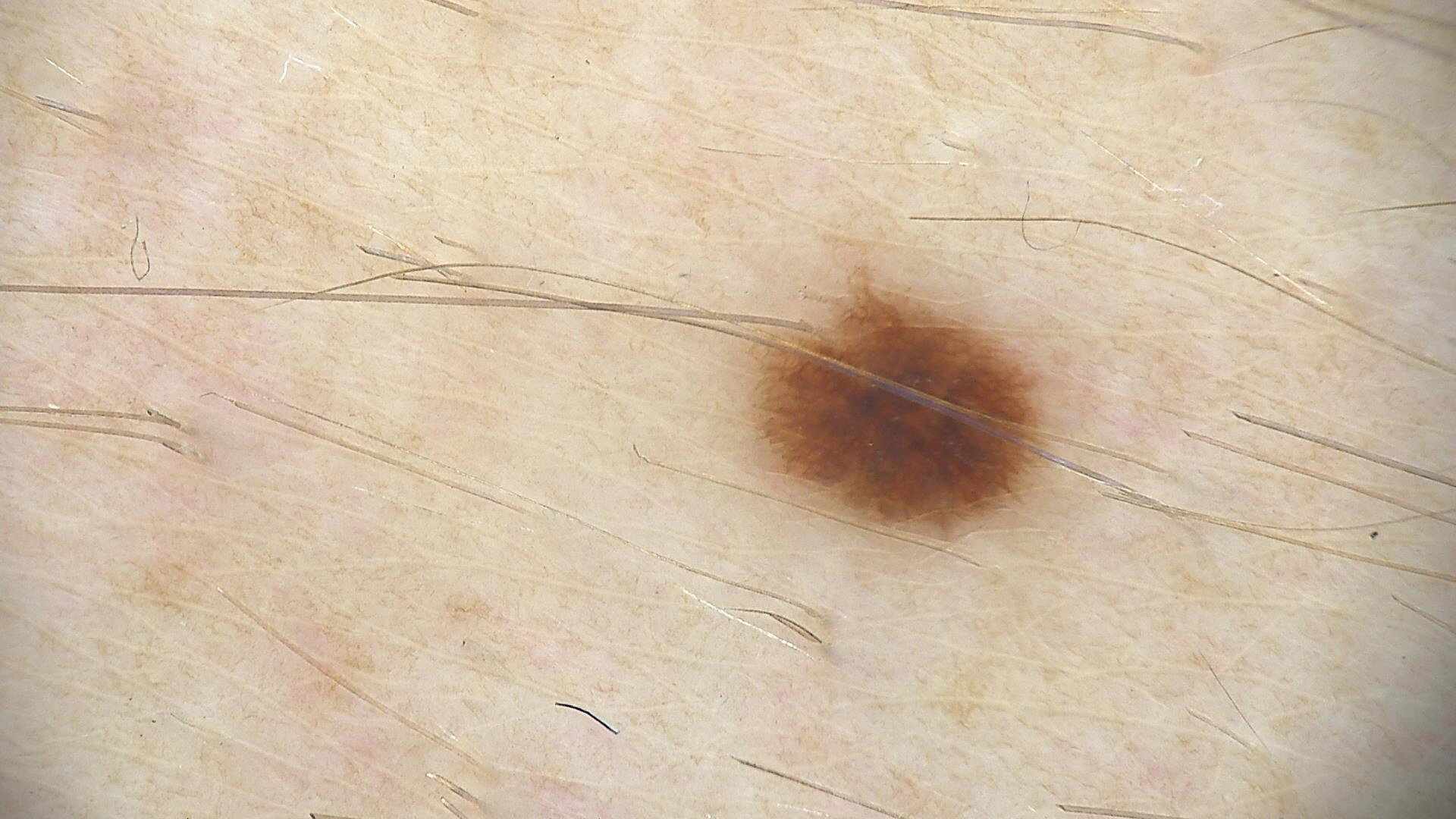Consistent with a dysplastic junctional nevus.